Close-up view. Female contributor, age 50–59. Located on the arm — 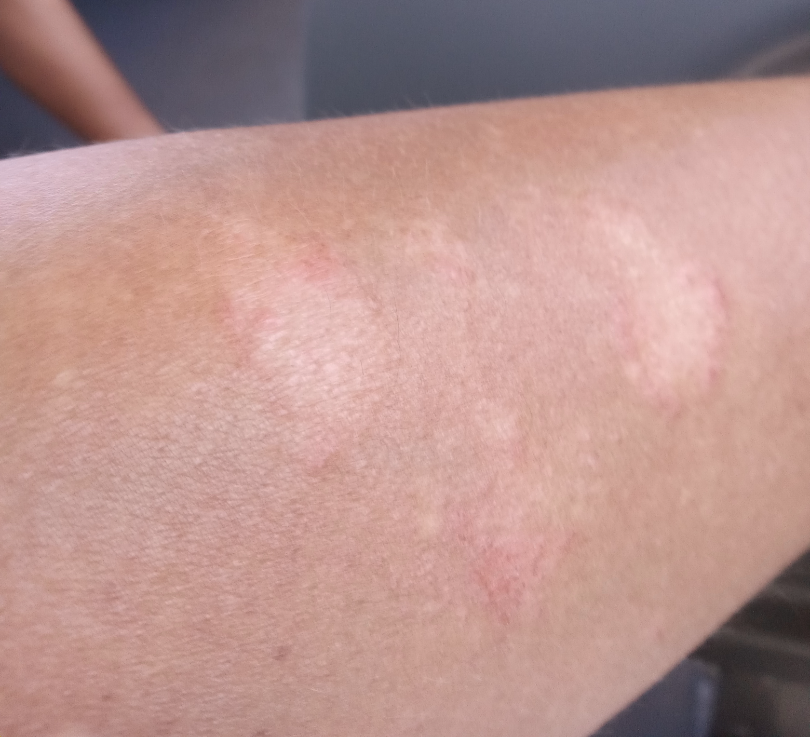patient describes the issue as = a rash | symptoms = itching | lesion texture = flat and raised or bumpy | dermatologist impression = a single dermatologist reviewed the case: the favored diagnosis is Tinea; possibly Granuloma annulare; a more distant consideration is Eczema.